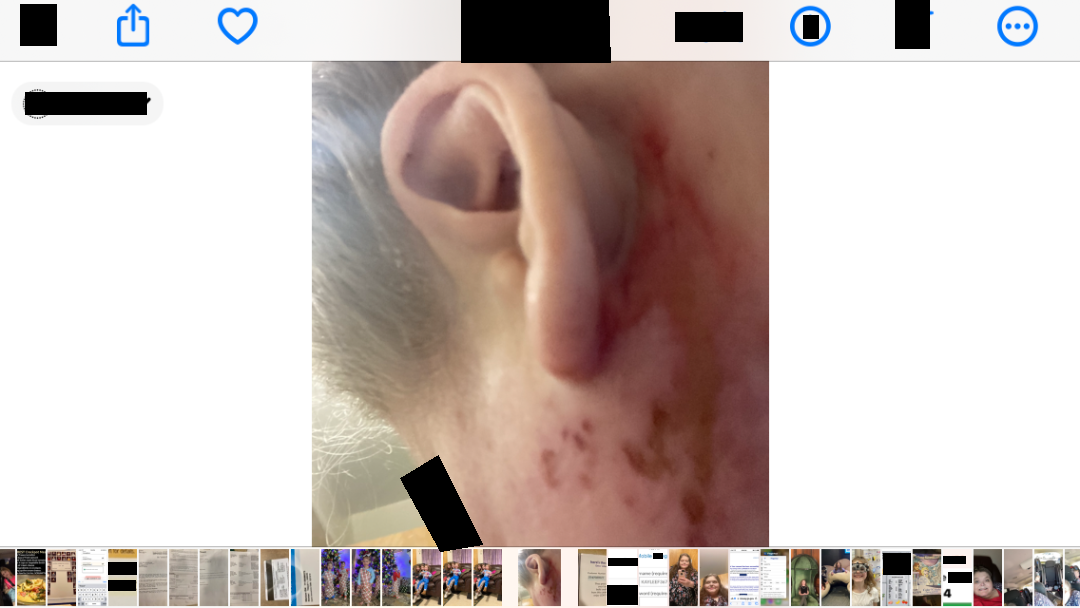assessment: unable to determine.